The photograph was taken at an angle, located on the front of the torso and leg, the patient considered this a rash, texture is reported as raised or bumpy, reported lesion symptoms include itching and enlargement:
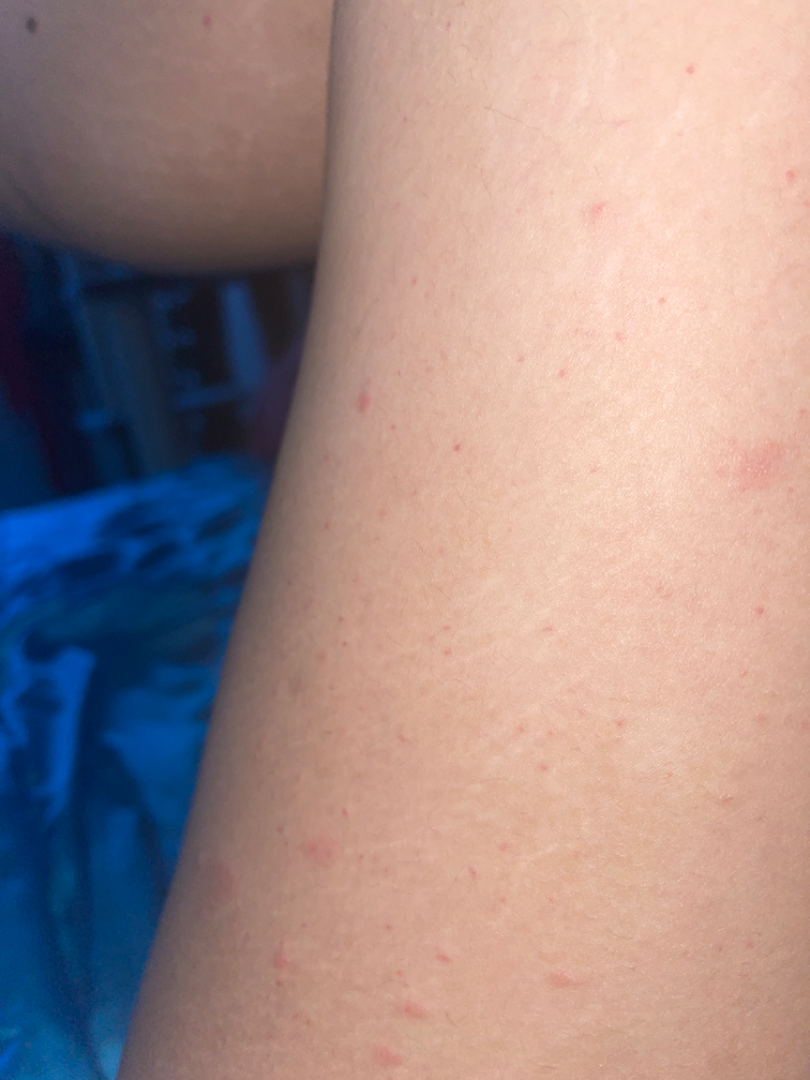Notes:
– dermatologist impression — three dermatologists independently reviewed the case: most consistent with Viral Exanthem; less likely is Pityriasis rosea; less probable is Allergic Contact Dermatitis; a more distant consideration is Drug Rash; lower on the differential is Hypersensitivity